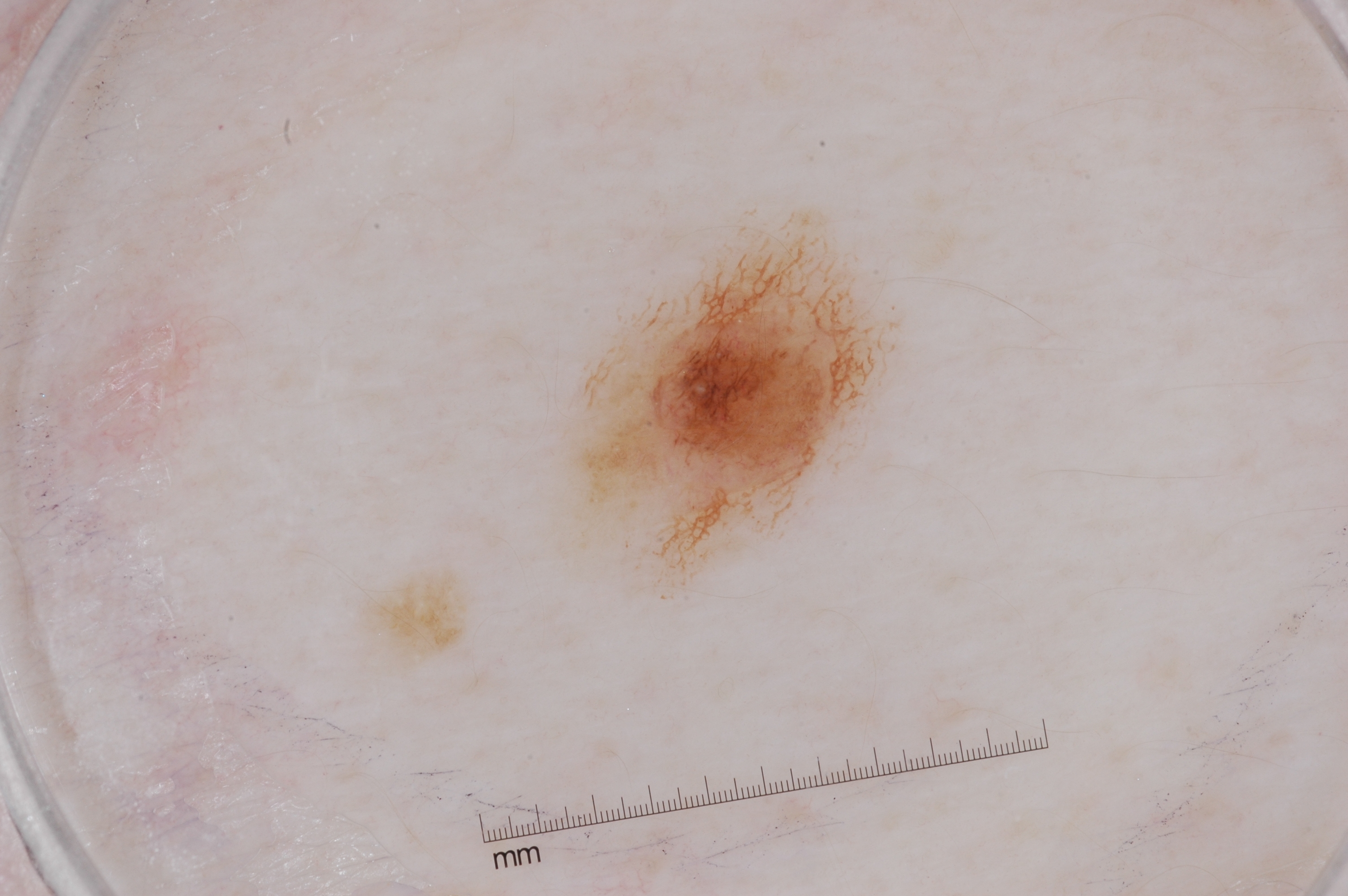Image and clinical context: A female patient, aged 43 to 47. A dermoscopic image of a skin lesion. As (left, top, right, bottom), the lesion's extent is [569,224,885,581]. Dermoscopy demonstrates pigment network. Impression: The diagnostic assessment was a melanocytic nevus.